The photograph is a close-up of the affected area.
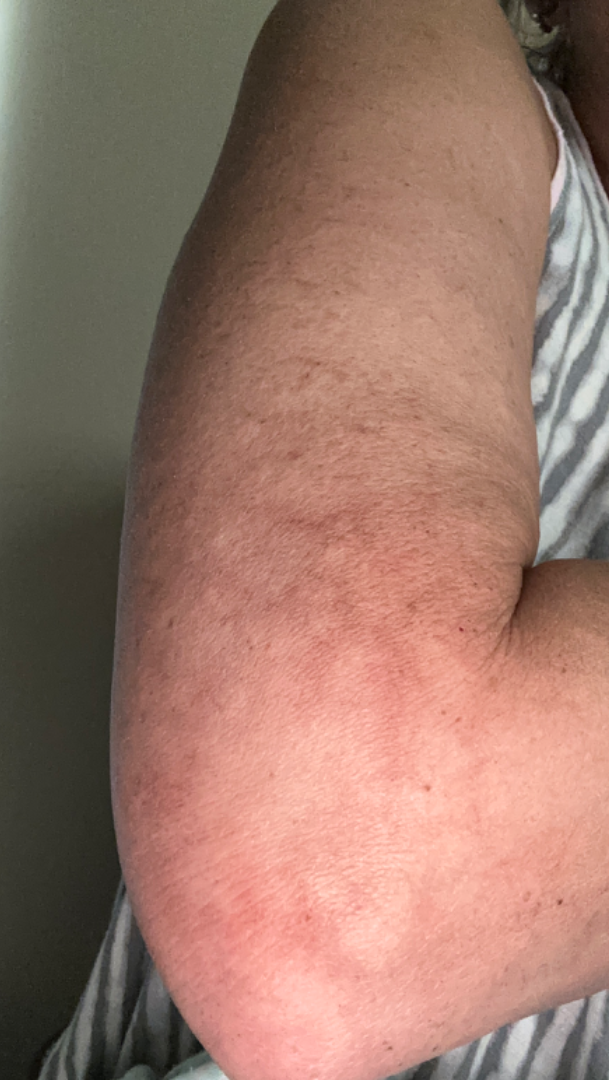Findings:
* assessment: could not be assessed